The leg and back of the torso are involved · the photo was captured at an angle · the contributor is male:
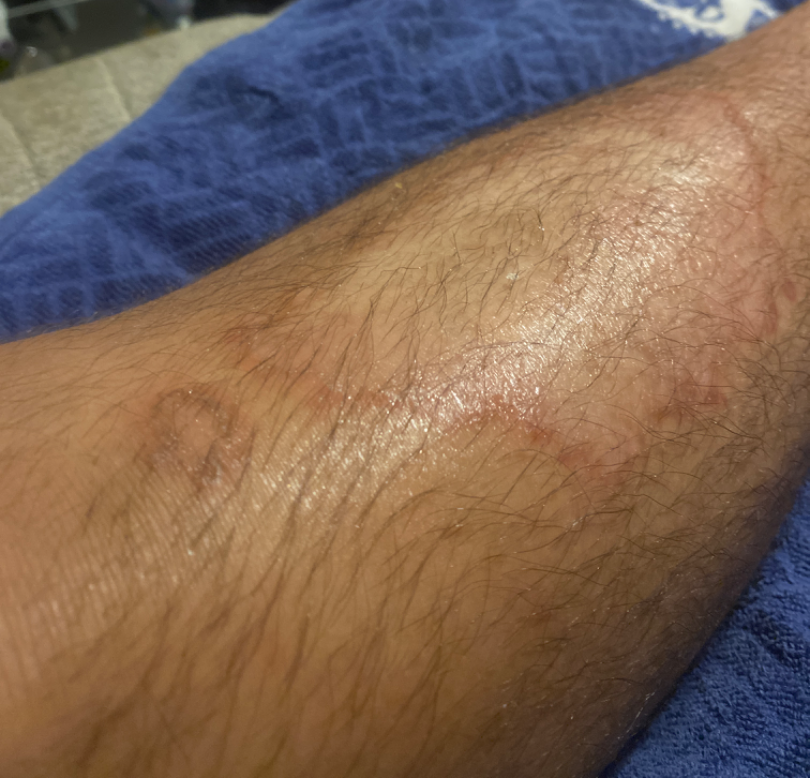{
  "differential": {
    "Necrobiosis lipoidica": 0.35,
    "Tinea": 0.22,
    "Porokeratosis": 0.21,
    "Eczema": 0.13,
    "Lichen sclerosus": 0.09
  }
}